Acquired for a research image collection, with no referral diagnosis; a male subject 73 years of age; a dermoscopy image of a skin lesion.
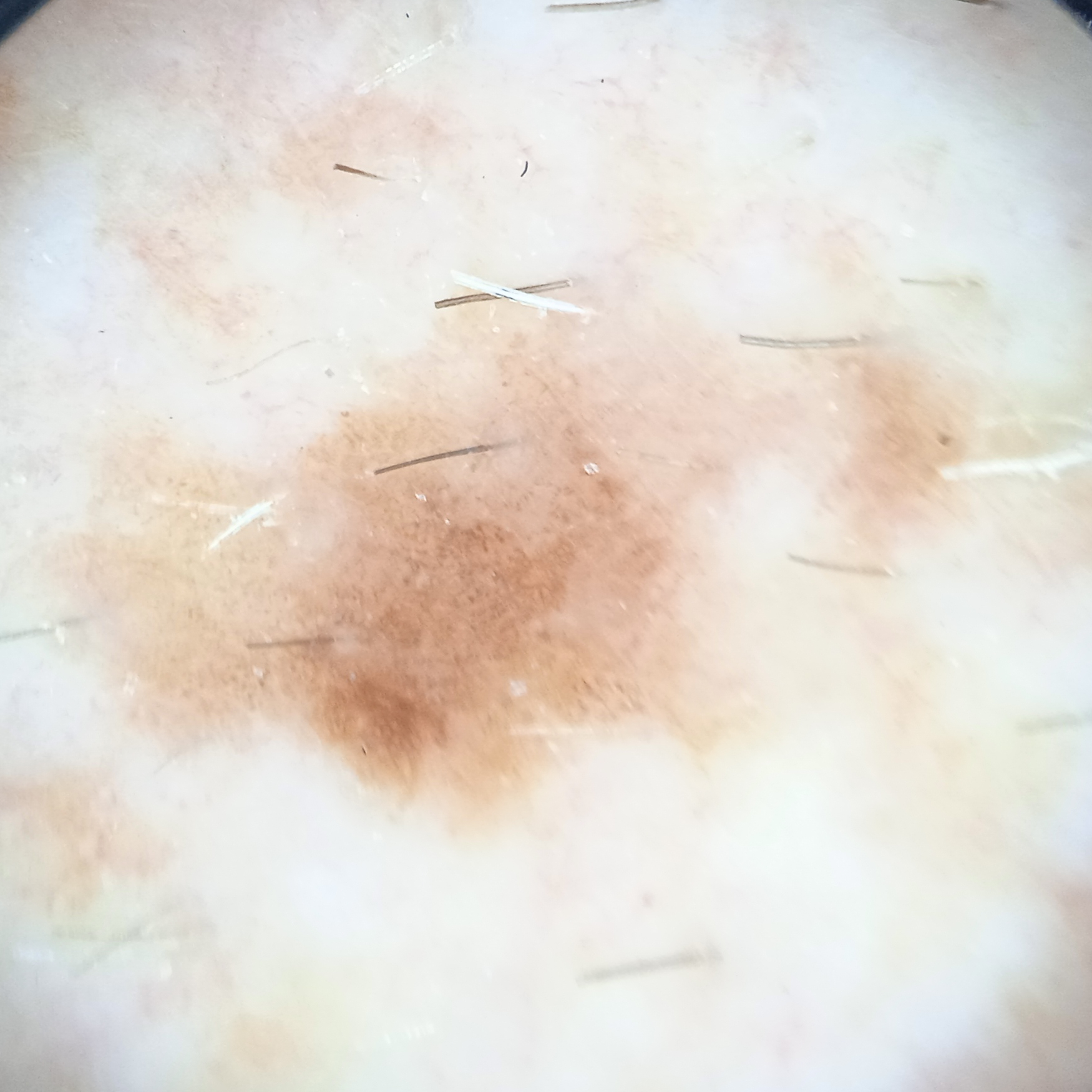The lesion measures approximately 6.6 mm. The dermatologists' assessment was a melanoma.